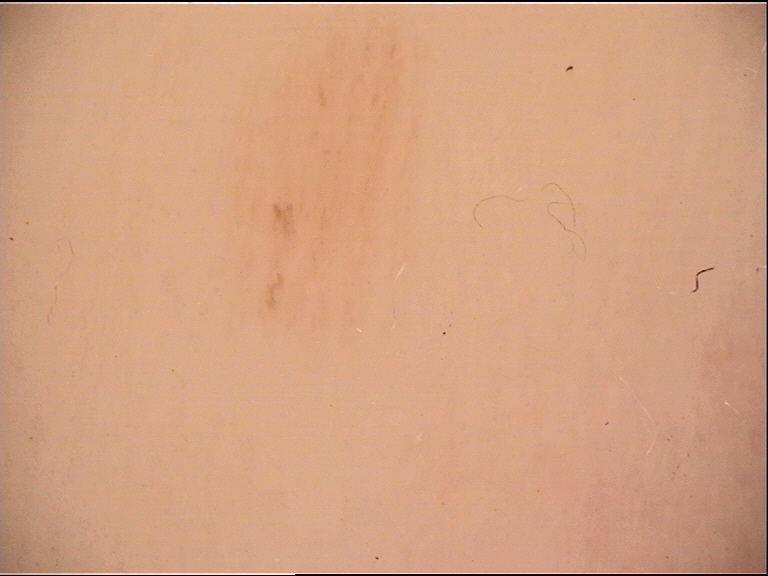Dermoscopy of a skin lesion. Consistent with a banal lesion — an acral junctional nevus.